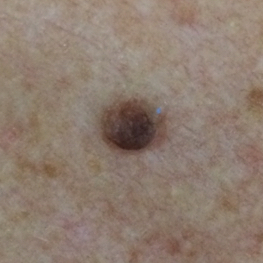subject: 56 years old
image: clinical photo
site: the chest
symptoms: elevation, growth
impression: nevus (clinical consensus)